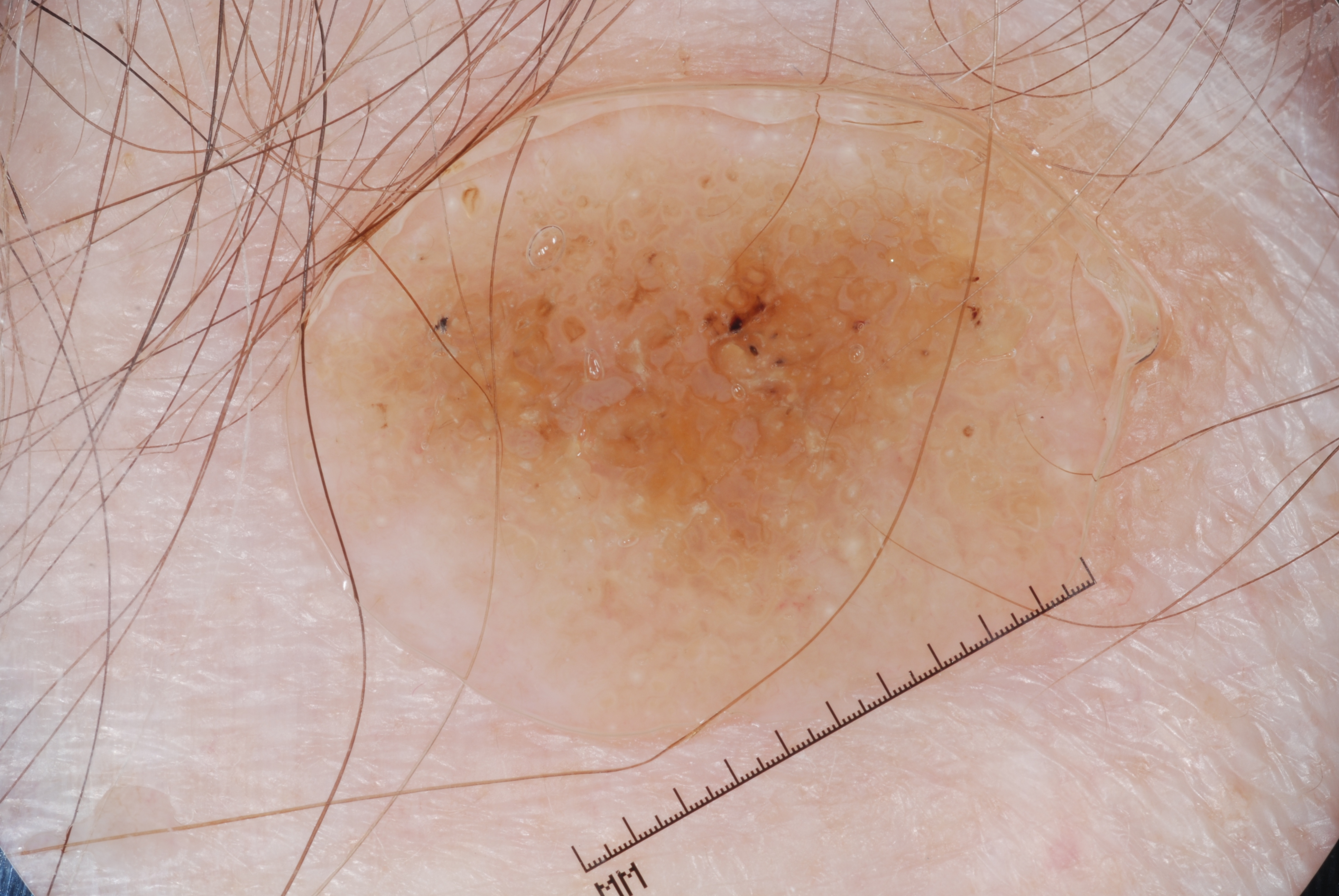A dermoscopic view of a skin lesion.
The patient is a female about 80 years old.
The lesion is bounded by x1=309, y1=43, x2=1144, y2=726.
The lesion takes up a large portion of the image.
On dermoscopy, the lesion shows milia-like cysts, with no negative network, pigment network, or streaks.
The diagnostic assessment was a seborrheic keratosis, a benign lesion.